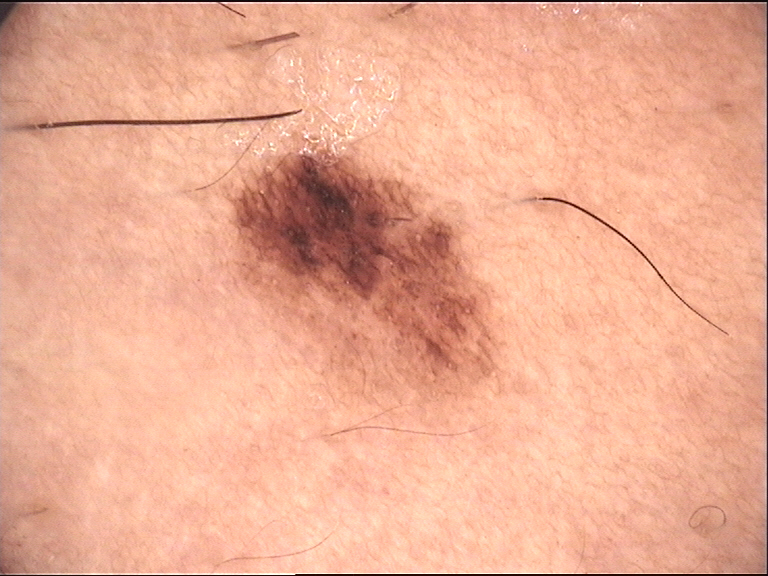imaging: dermatoscopy, label: dysplastic junctional nevus (expert consensus).